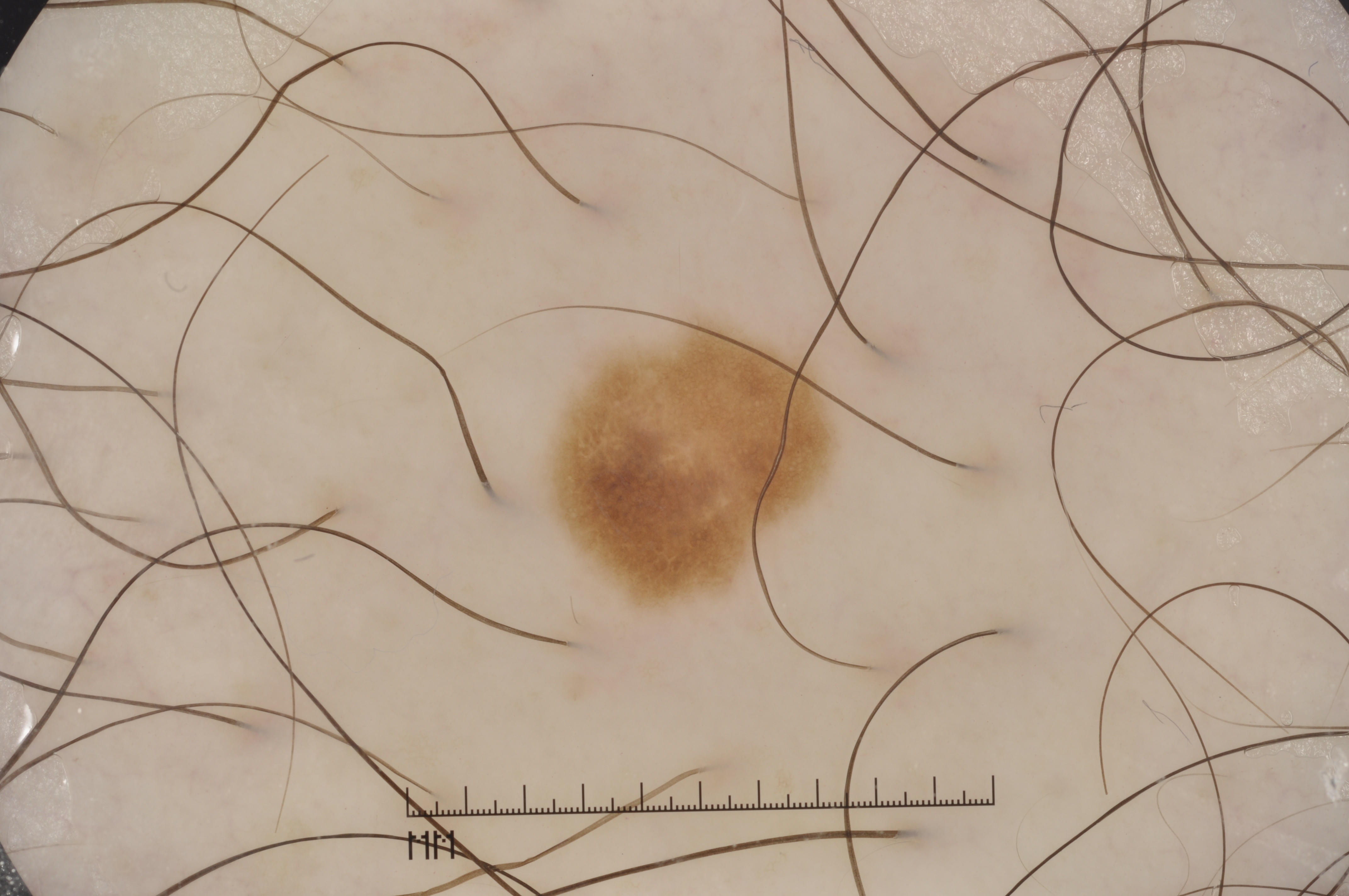Findings:
A male subject approximately 40 years of age. A dermatoscopic image of a skin lesion. The lesion occupies roughly 6% of the field. The lesion is located at <bbox>543, 306, 836, 620</bbox>. Dermoscopic examination shows negative network and pigment network, with no streaks or milia-like cysts.
Conclusion:
Consistent with a melanocytic nevus.